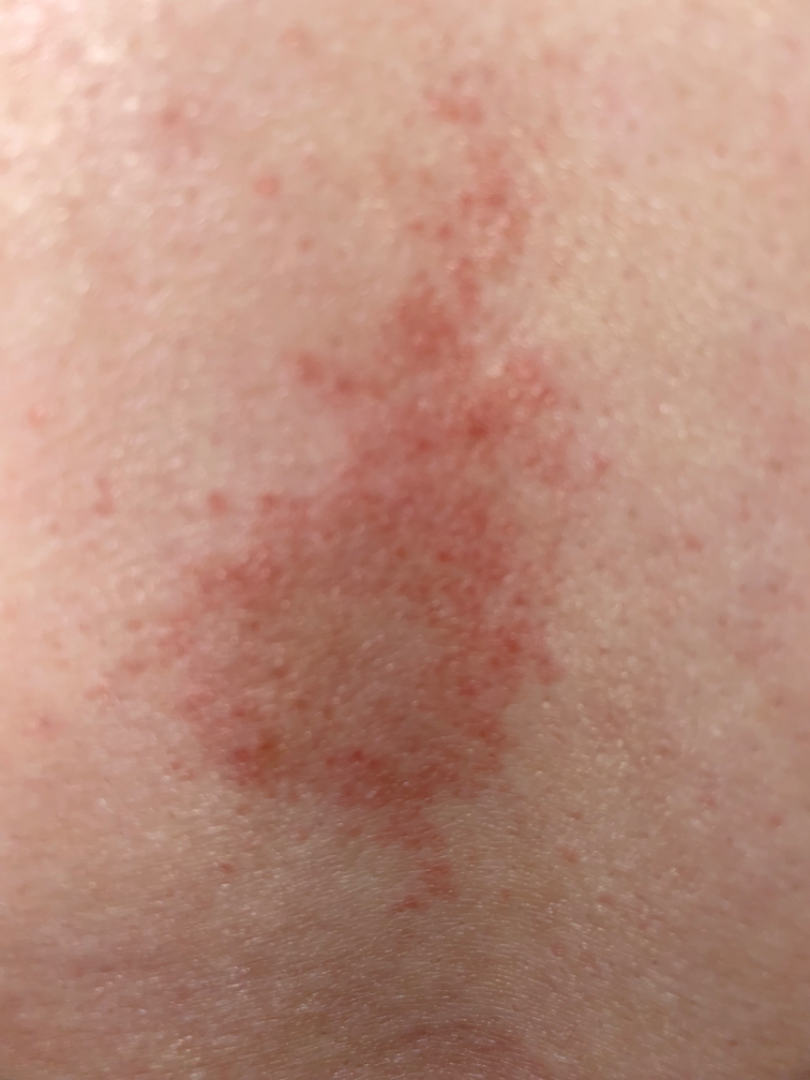self-categorized as = a rash
affected area = back of the torso
framing = close-up
other reported symptoms = none reported
symptoms = bothersome appearance and itching
surface texture = flat
contributor = female, age 30–39
diagnostic considerations = most likely Eczema; the differential also includes Allergic Contact Dermatitis; less likely is Psoriasis